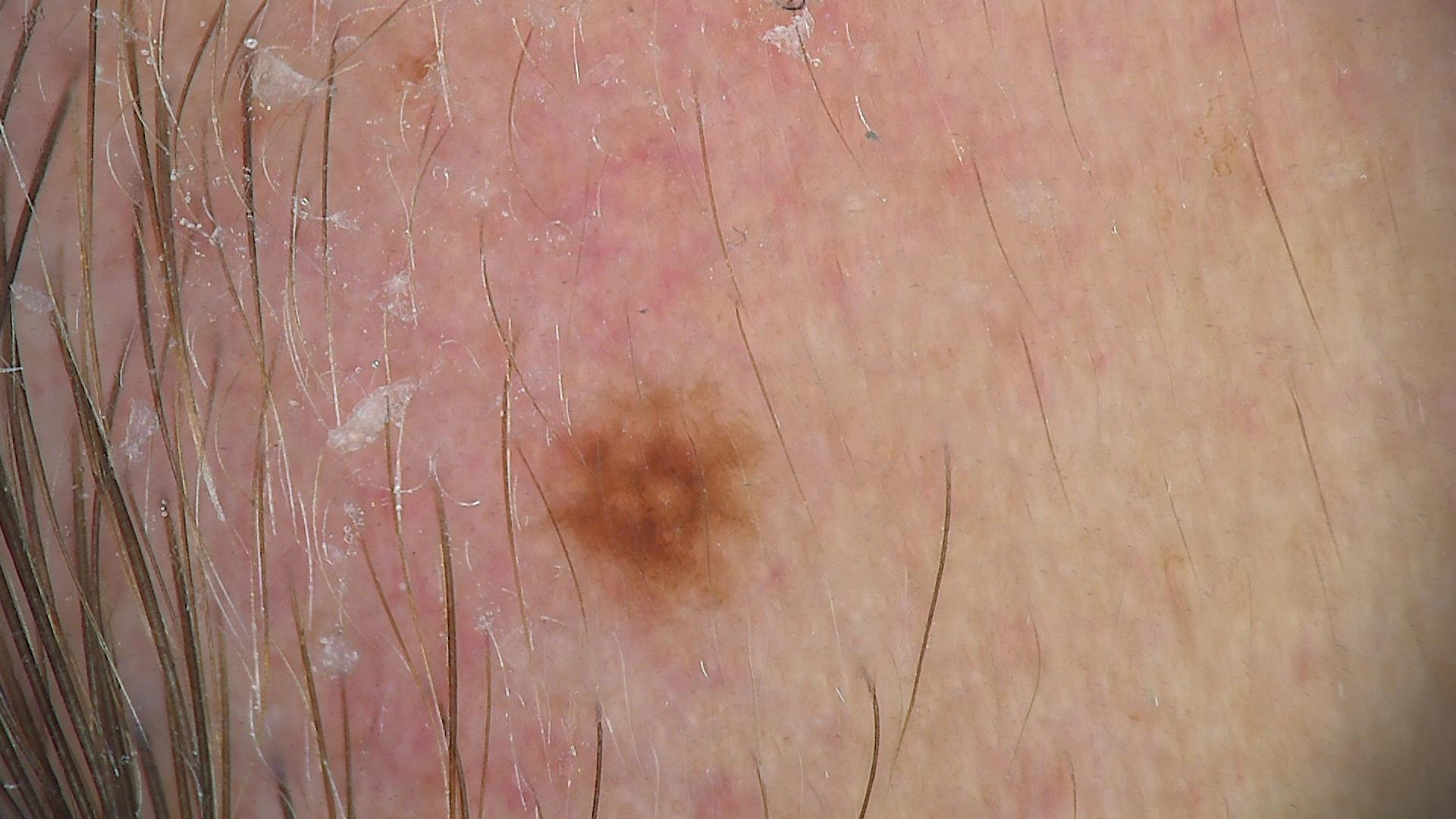Classified as a dysplastic compound nevus.